The affected area is the arm; the photograph is a close-up of the affected area — 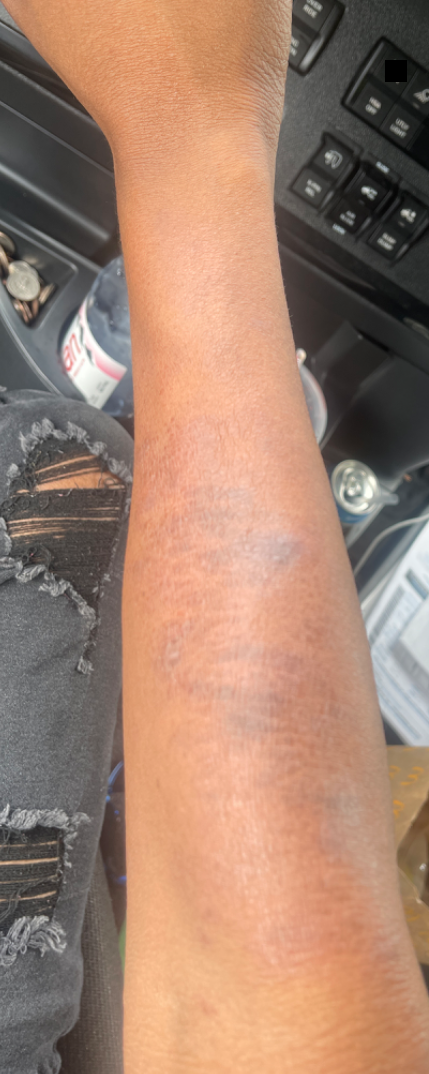{
  "assessment": "ungradable on photographic review",
  "symptoms": [
    "darkening",
    "itching"
  ],
  "texture": [
    "raised or bumpy",
    "rough or flaky"
  ],
  "patient_category": "a rash"
}